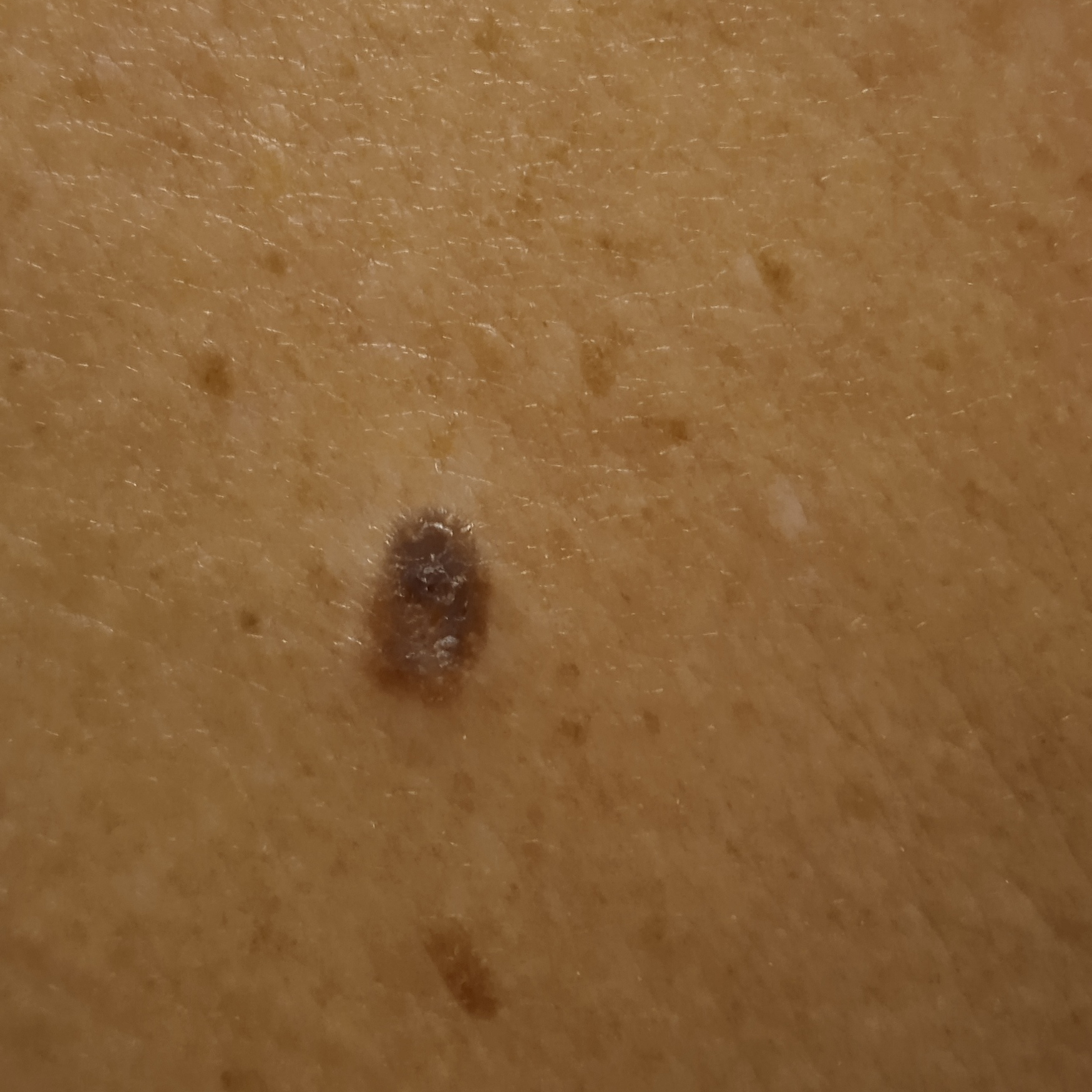| field | value |
|---|---|
| sun reaction | skin tans without first burning |
| patient | male, 72 years old |
| modality | clinical photo |
| clinical context | research study (no referral diagnosis) |
| nevus count | a moderate number of melanocytic nevi |
| body site | the back |
| size | 8.1 mm |
| diagnostic label | seborrheic keratosis (dermatologist consensus) |